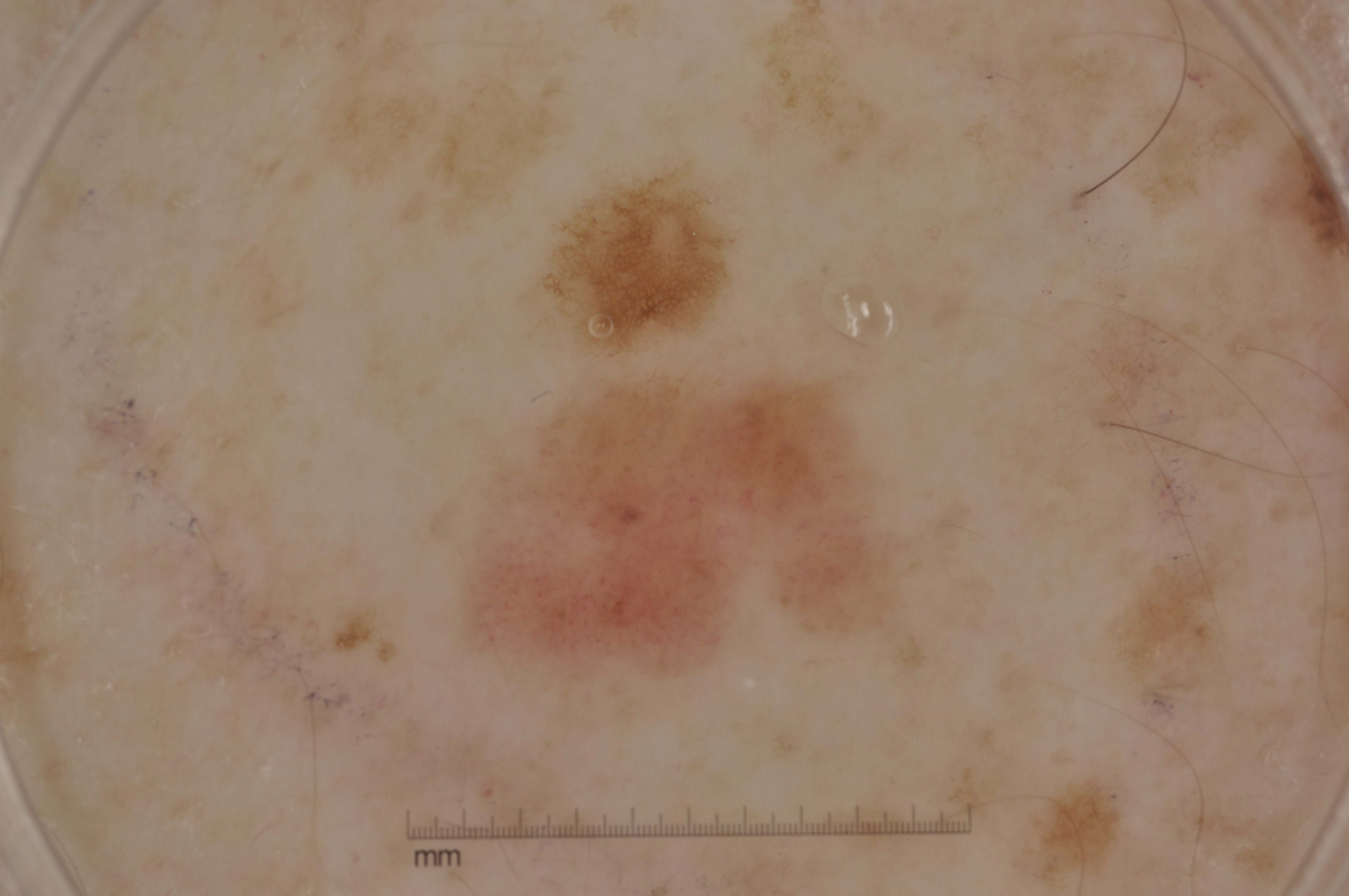Q: What kind of image is this?
A: dermoscopy
Q: Where is the lesion located?
A: 440, 325, 952, 740
Q: How large is the lesion within the image?
A: moderate
Q: Which assessed dermoscopic features were absent?
A: negative network, pigment network, milia-like cysts, and streaks
Q: What is the diagnosis?
A: a melanoma, a malignant lesion